Close-up view, the top or side of the foot is involved:
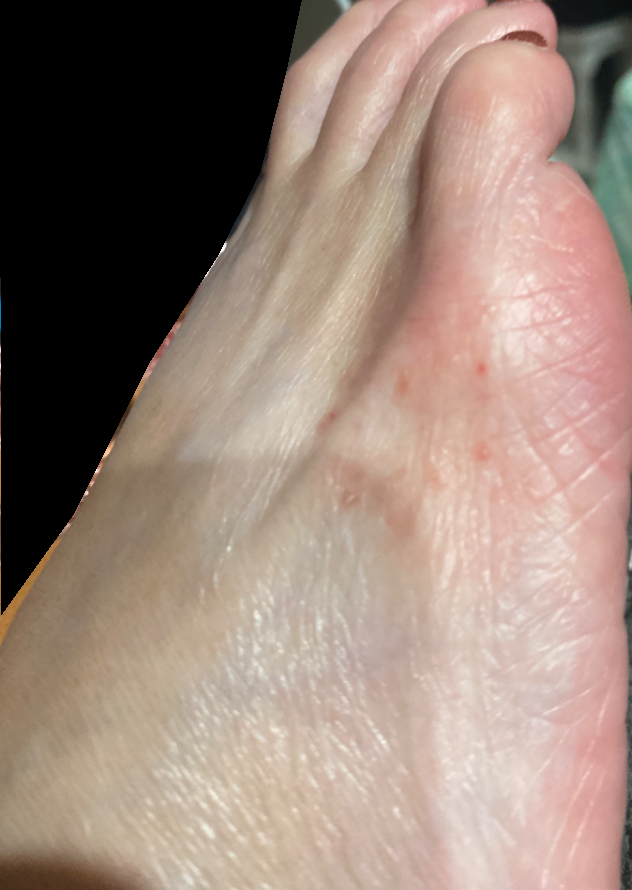History: The patient described the issue as a rash. Skin tone: lay graders estimated MST 2. The contributor notes the lesion is raised or bumpy. The contributor notes the condition has been present for one to four weeks. Impression: The reviewing dermatologist's impression was: Eczema (weight 0.67); Tinea (weight 0.33).